A dermoscopic image of a skin lesion:
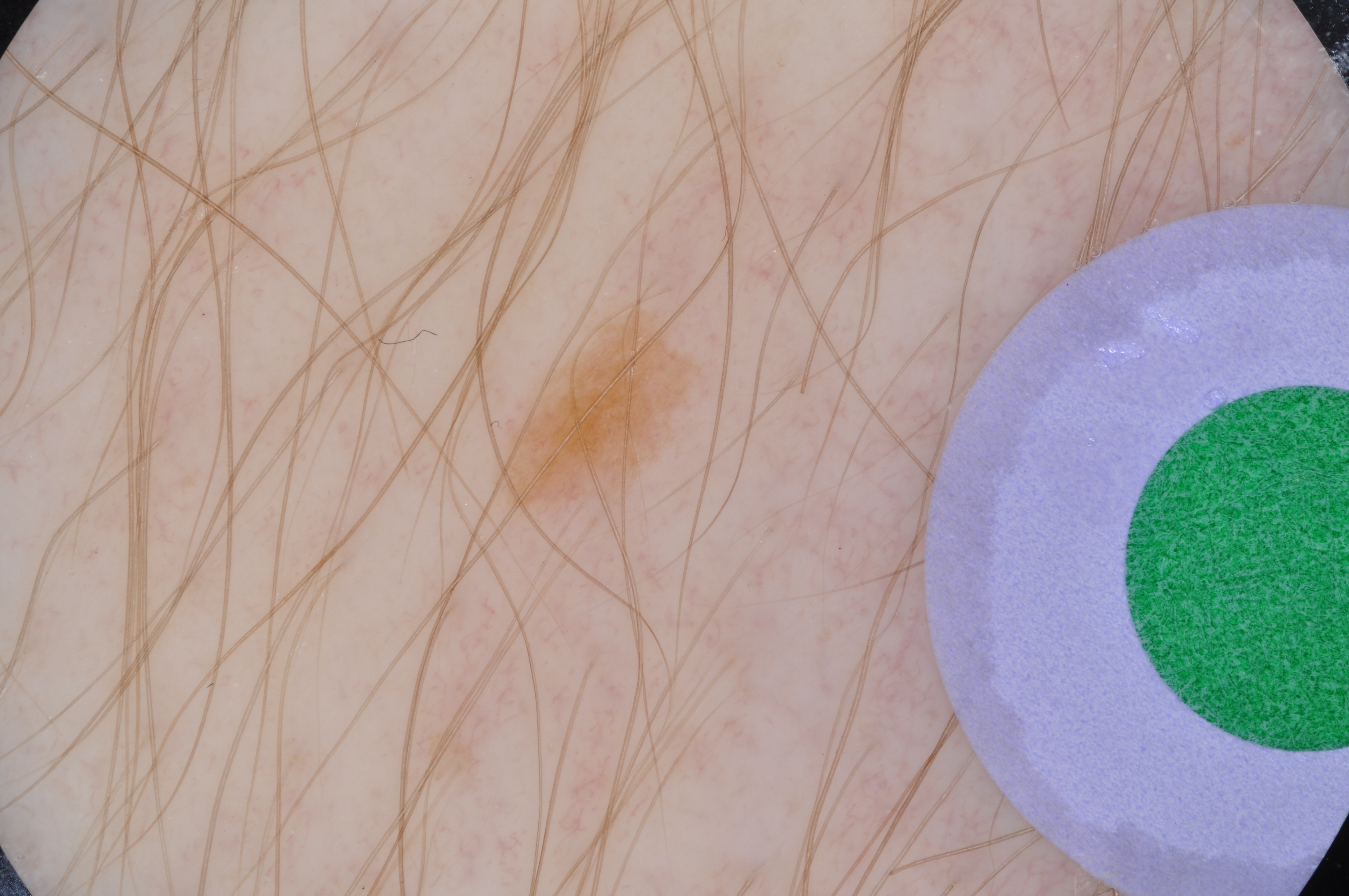Summary: Dermoscopic assessment notes neither streaks nor globules. A small lesion within a wider field of skin. In (x1, y1, x2, y2) order, the visible lesion spans bbox(493, 298, 713, 527). Conclusion: Diagnosed as a benign lesion.